A smartphone photograph of a skin lesion:
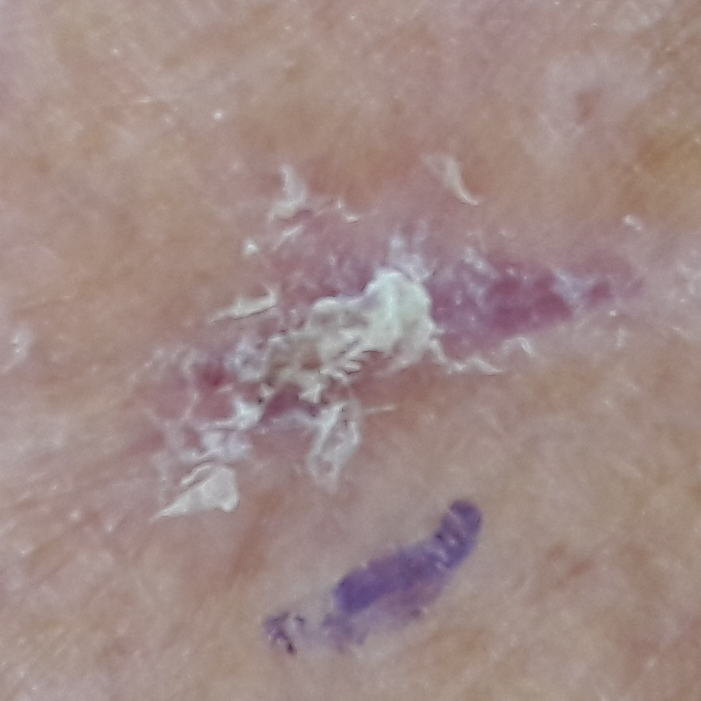By the patient's account, the lesion has not grown and has not changed. Consistent with a premalignant lesion — an actinic keratosis.